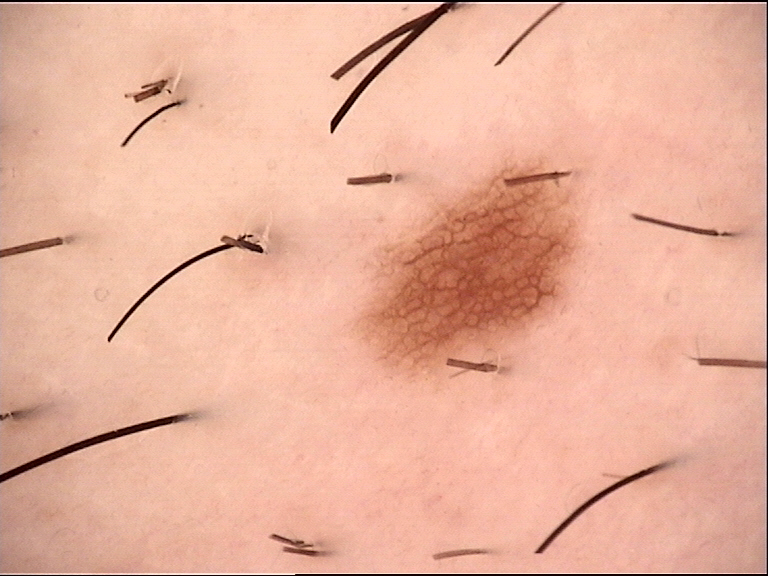A skin lesion imaged with a dermatoscope.
Diagnosed as a benign lesion — a dysplastic junctional nevus.